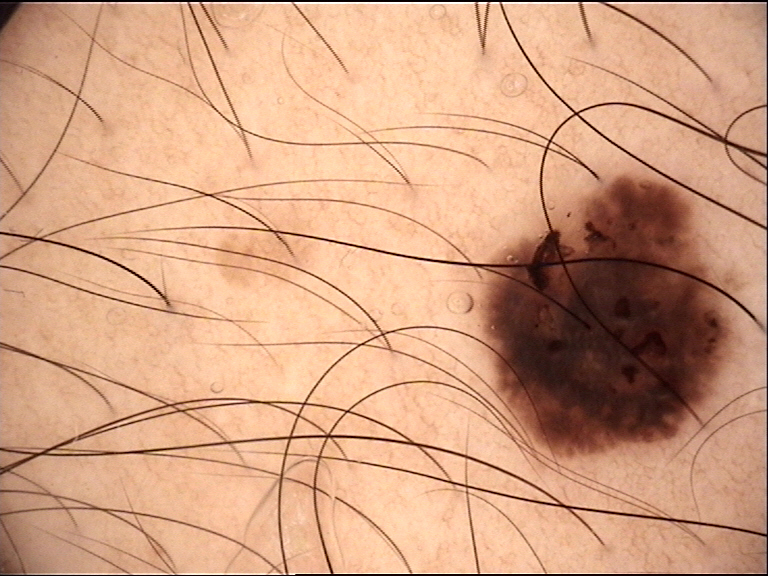Confirmed on histopathology as a melanoma.